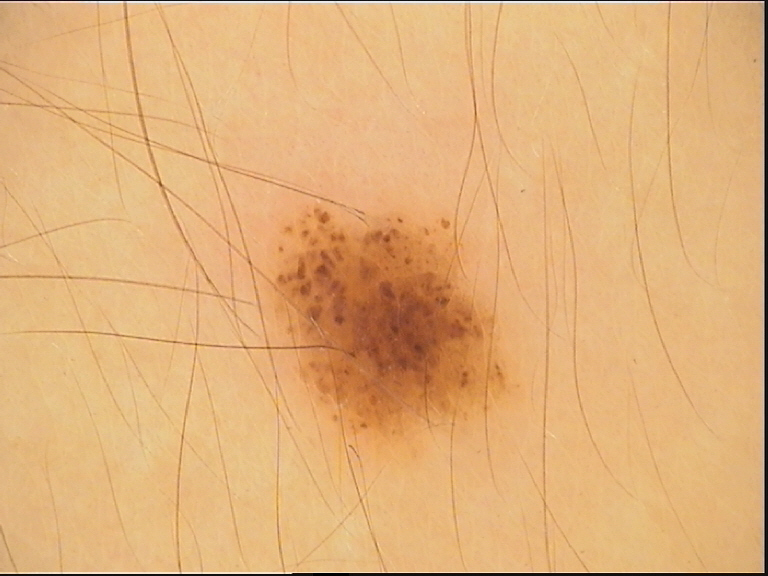Labeled as a dysplastic junctional nevus.